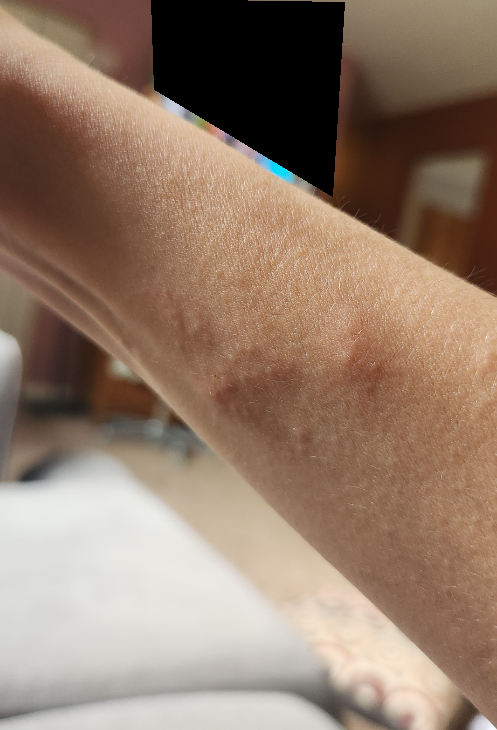Patient information:
An image taken at an angle. Symptoms reported: burning and itching. Fitzpatrick phototype II. Female subject, age 30–39. The patient described the issue as a rash. The patient indicates the lesion is raised or bumpy. No relevant systemic symptoms. The patient indicates the condition has been present for less than one week.
Review:
A single dermatologist reviewed the case: the leading consideration is Koebner phenomenon; also consider Molluscum Contagiosum; lower on the differential is Viral Exanthem.